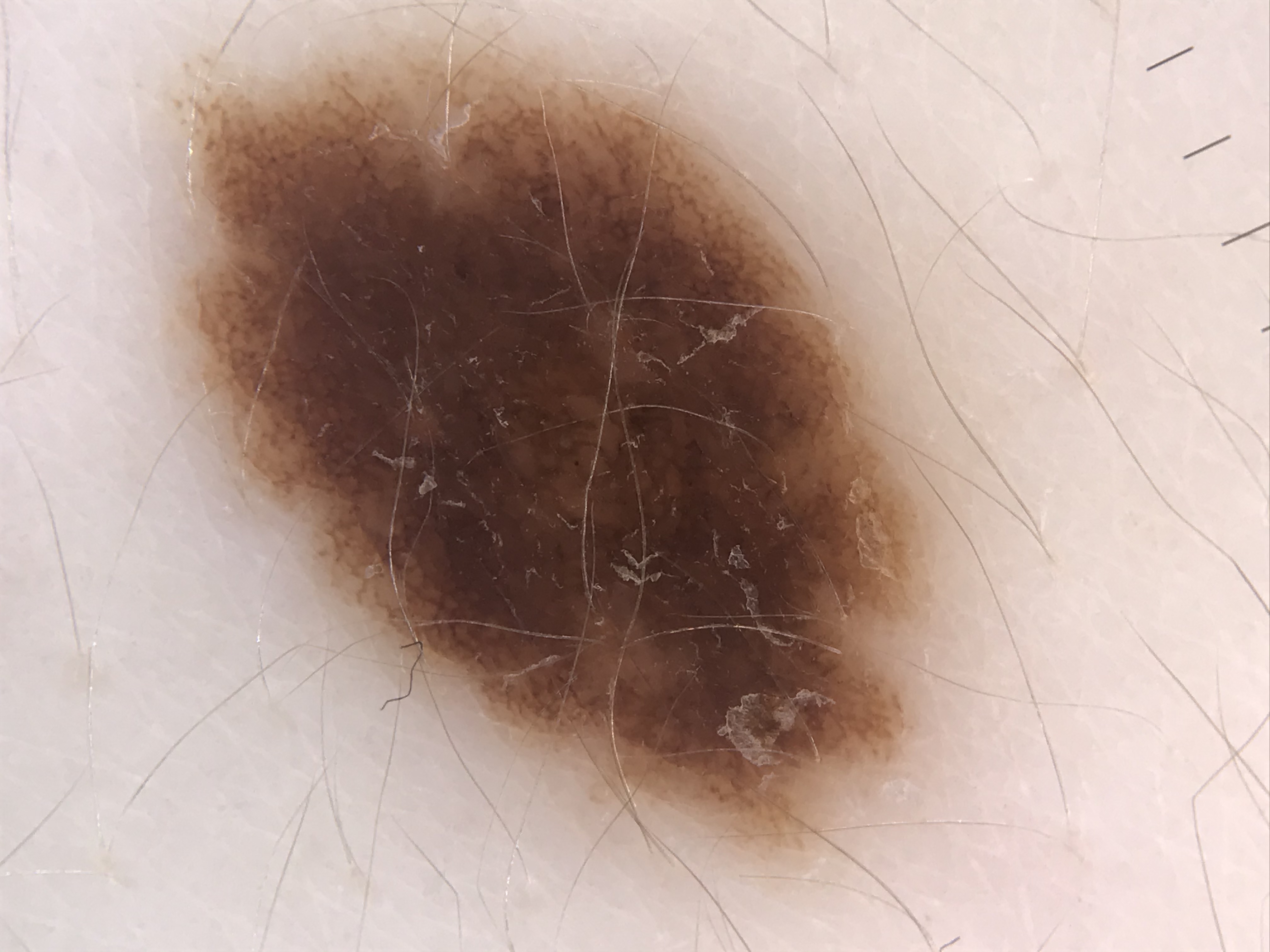A dermatoscopic image of a skin lesion.
The diagnostic label was a dysplastic compound nevus.